A clinical close-up of a skin lesion; imaged for a research study, with no referral diagnosis recorded; a male subject aged 62: 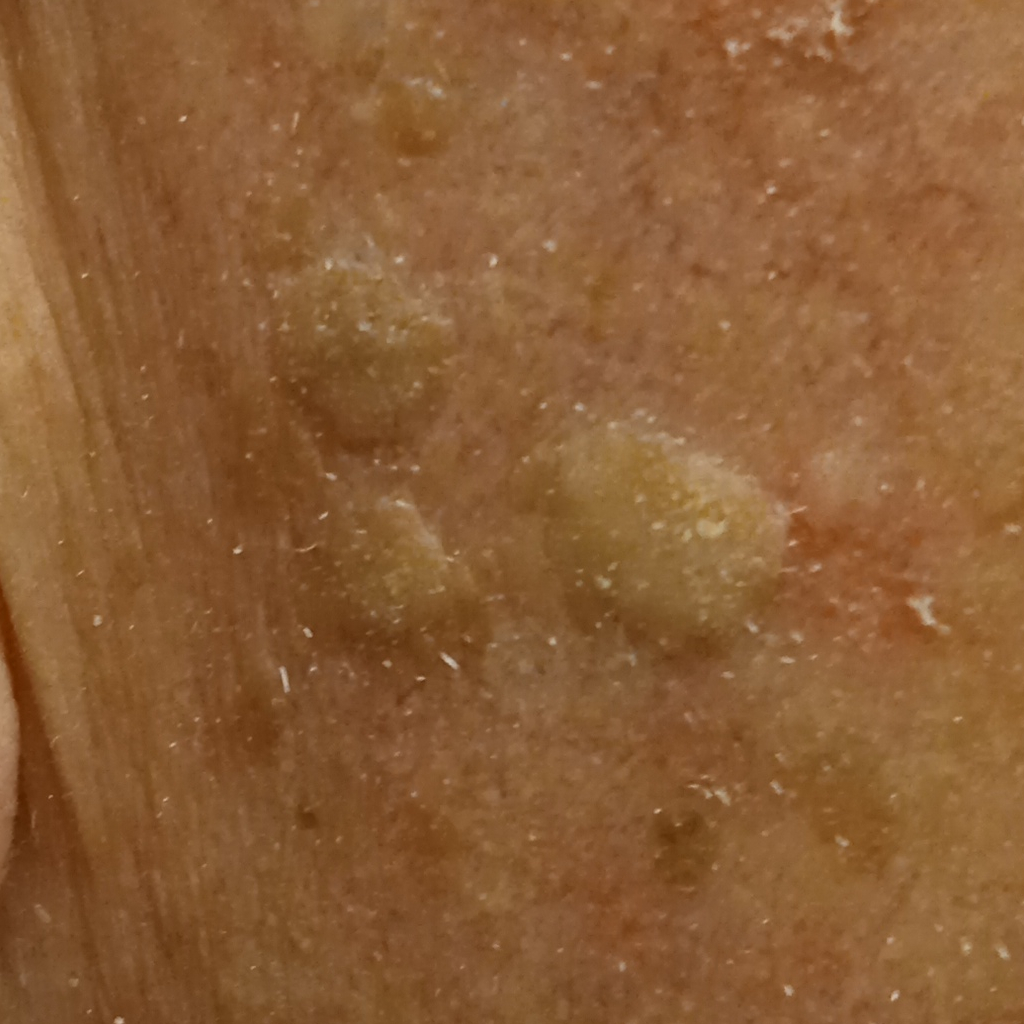* site — the face
* diameter — 7.5 mm
* assessment — seborrheic keratosis (dermatologist consensus)